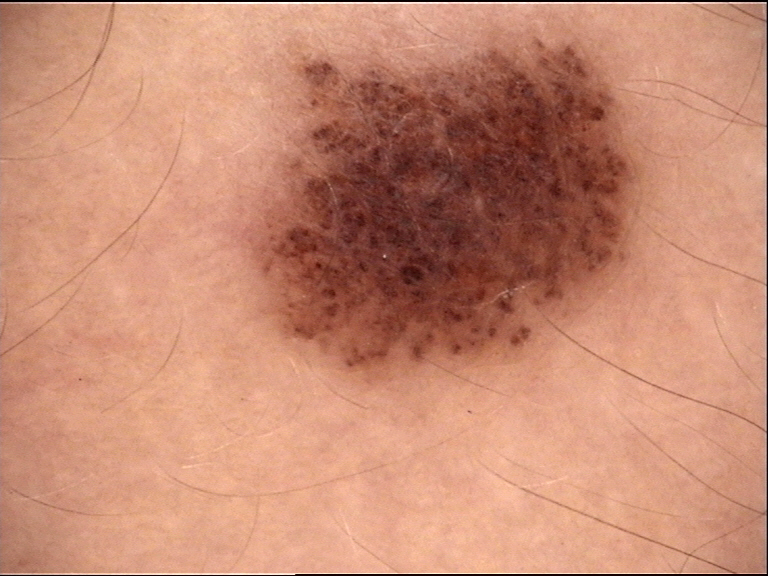image: dermatoscopy
diagnosis:
  name: dysplastic junctional nevus
  code: jd
  malignancy: benign
  super_class: melanocytic
  confirmation: expert consensus